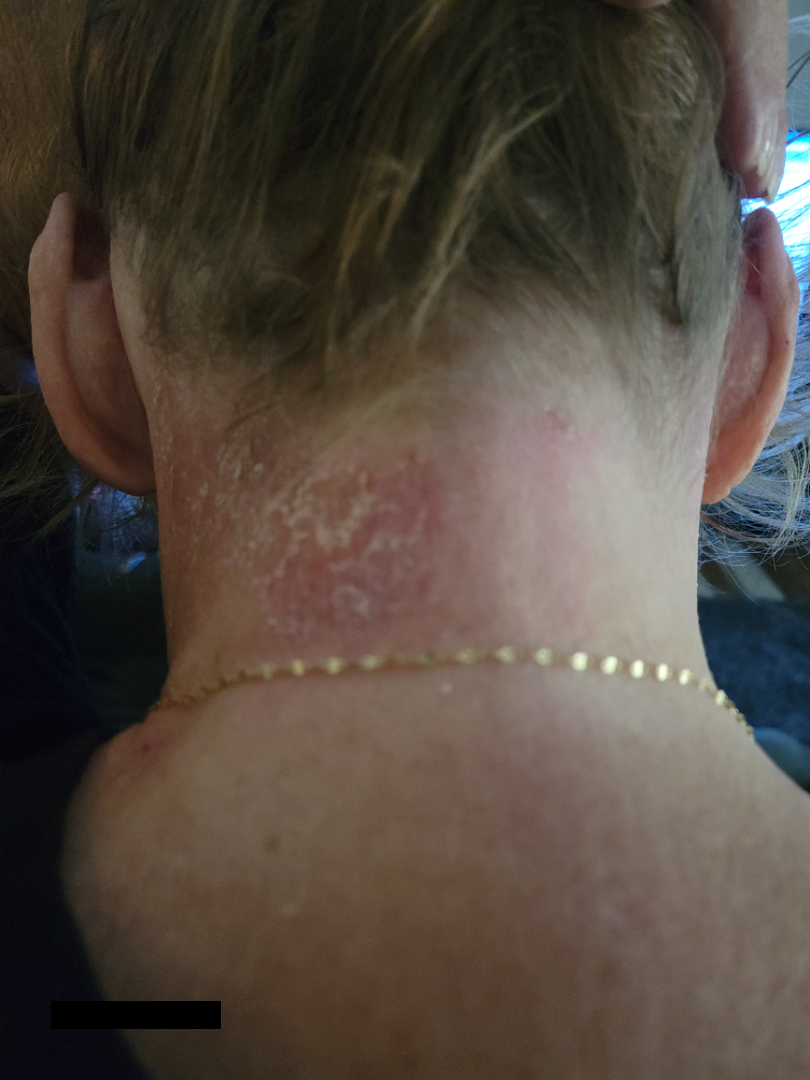Q: How was the photo taken?
A: close-up
Q: What is the dermatologist's impression?
A: the leading consideration is Psoriasis; also consider Eczema